By self-report, a family history of skin cancer and a history of sunbed use; few moles overall by the patient's own estimate; a female patient aged 48; a dermoscopic image of a skin lesion; the patient says their skin reddens painfully with sun exposure; the referring clinician suspected basal cell carcinoma — 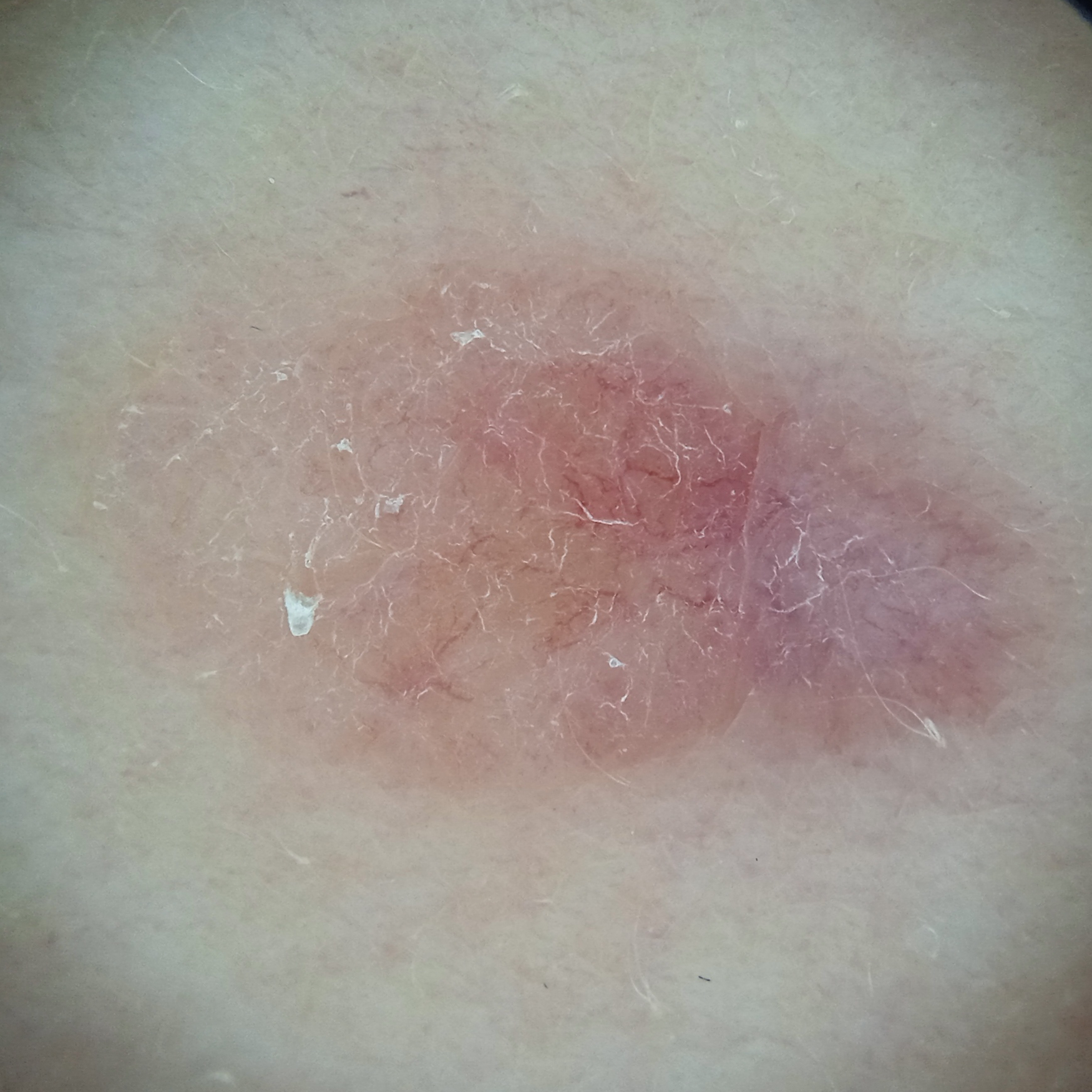The lesion is on the back. The lesion is about 12.3 mm across. Confirmed on histopathology as a basal cell carcinoma, following excision, with a measured tumor thickness of 1.1 mm.